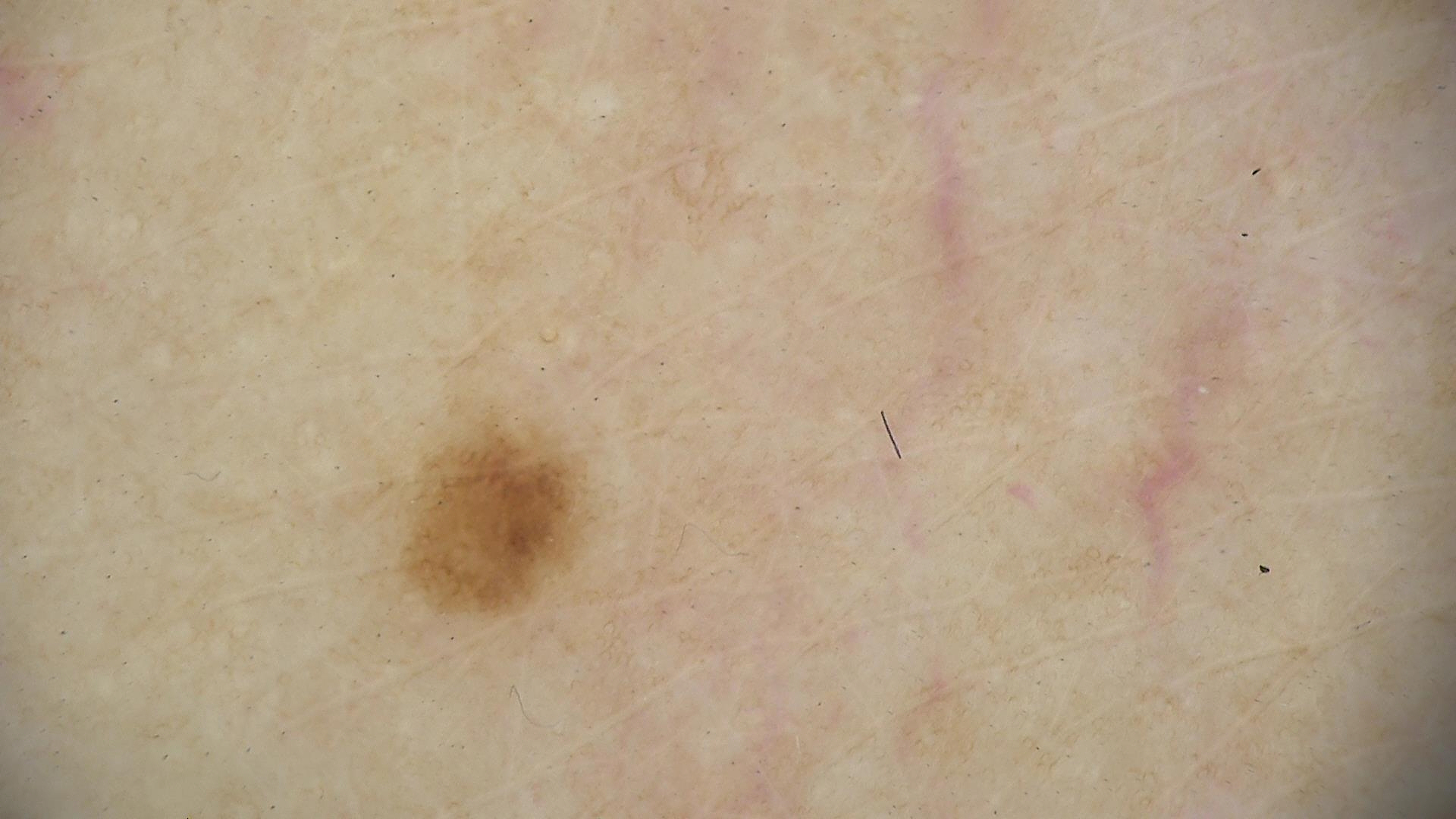image = dermatoscopy | subtype = banal | class = junctional nevus (expert consensus).